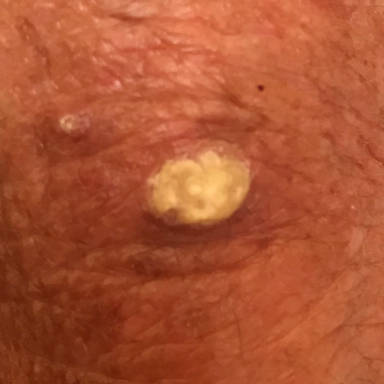A clinical photograph showing a skin lesion. A female subject 70 years old. The lesion is on an arm. The lesion measures approximately 10 × 6 mm. The biopsy diagnosis was a premalignant lesion — an actinic keratosis.